Imaged for a research study, with no referral diagnosis recorded; by self-report, a personal history of cancer; the patient describes having few moles overall; a clinical photograph showing a skin lesion; a female patient 84 years old:
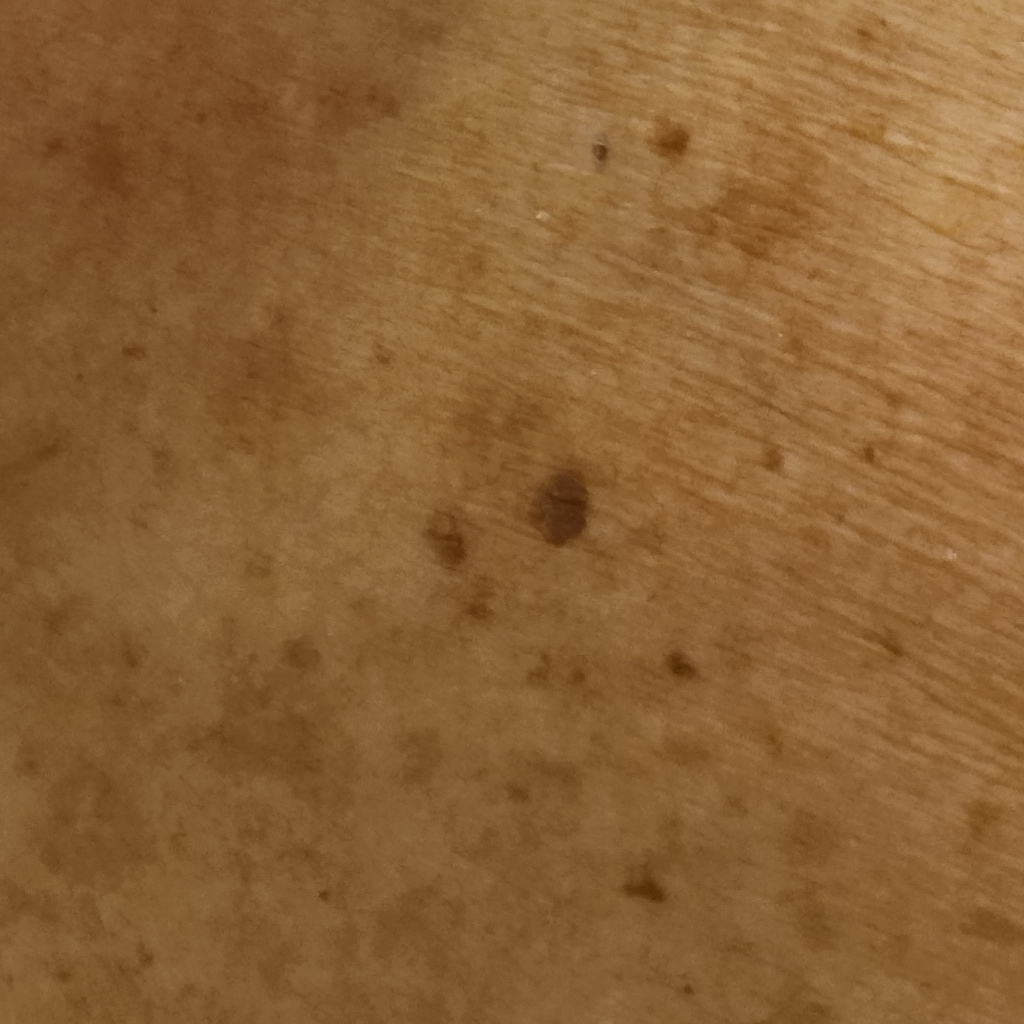| feature | finding |
|---|---|
| location | the torso |
| diameter | 4.6 mm |
| diagnosis | seborrheic keratosis (dermatologist consensus) |